Close-up view — 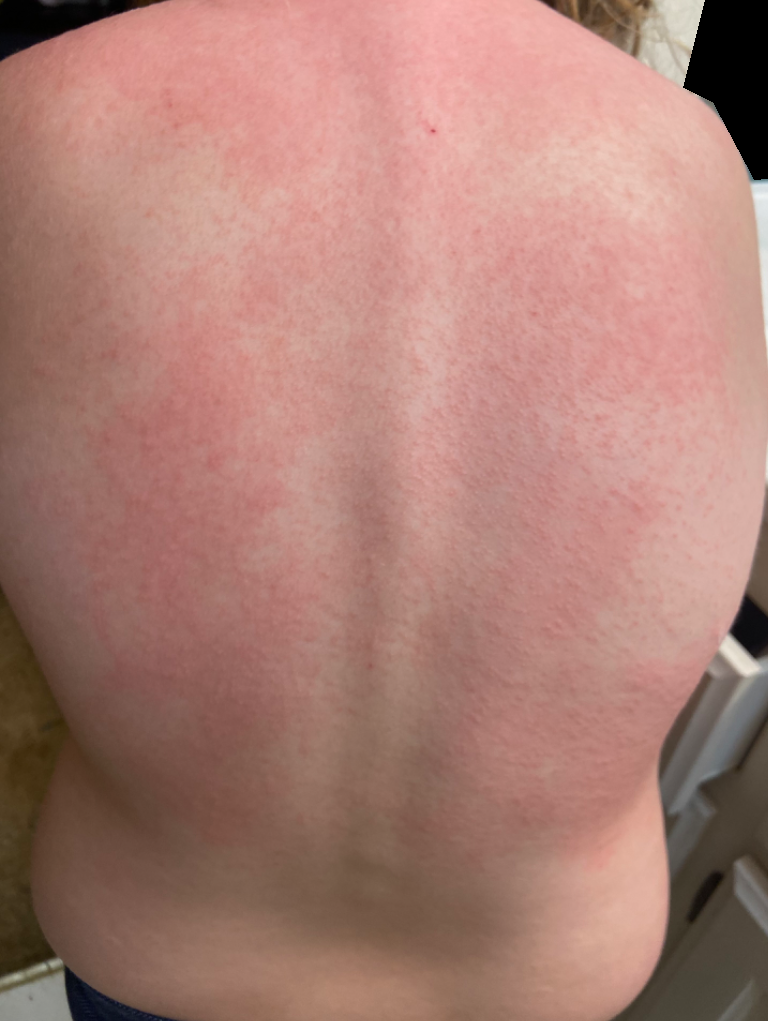differential:
  tied_lead:
    - Urticaria
    - Acute dermatitis, NOS
    - Allergic Contact Dermatitis